Dermoscopy of a skin lesion:
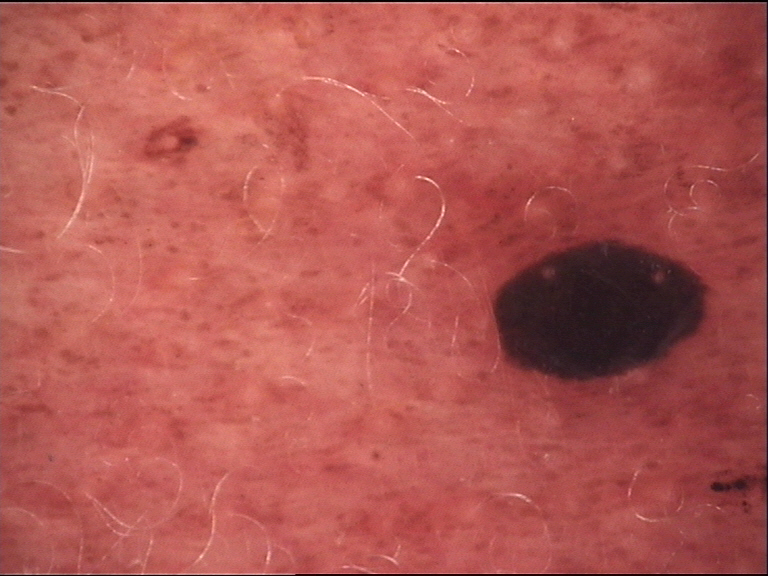The architecture is that of a banal lesion. Classified as a congenital compound nevus.